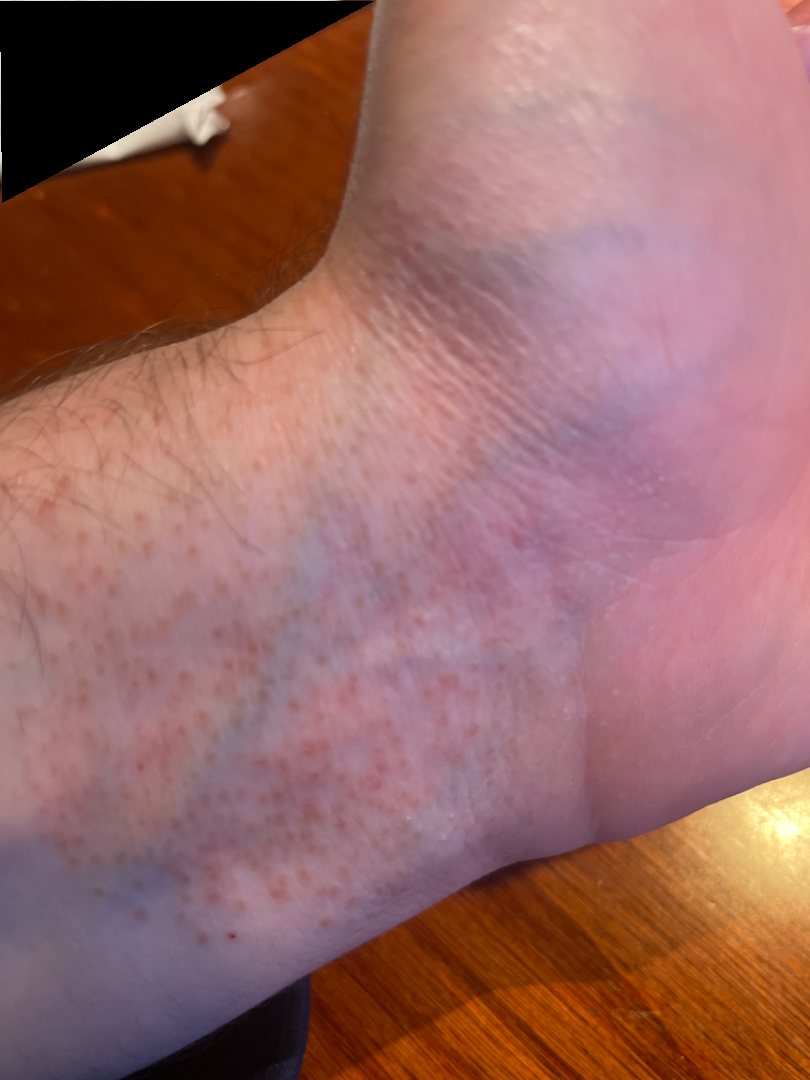A close-up photograph.
On dermatologist assessment of the image, most consistent with Eczema; also raised was Lichen planus/lichenoid eruption.